A clinical photograph showing a skin lesion; a male subject age 80; the chart notes prior skin cancer (patient or family), alcohol use, no tobacco use, and no pesticide exposure; the patient is Fitzpatrick skin type I: 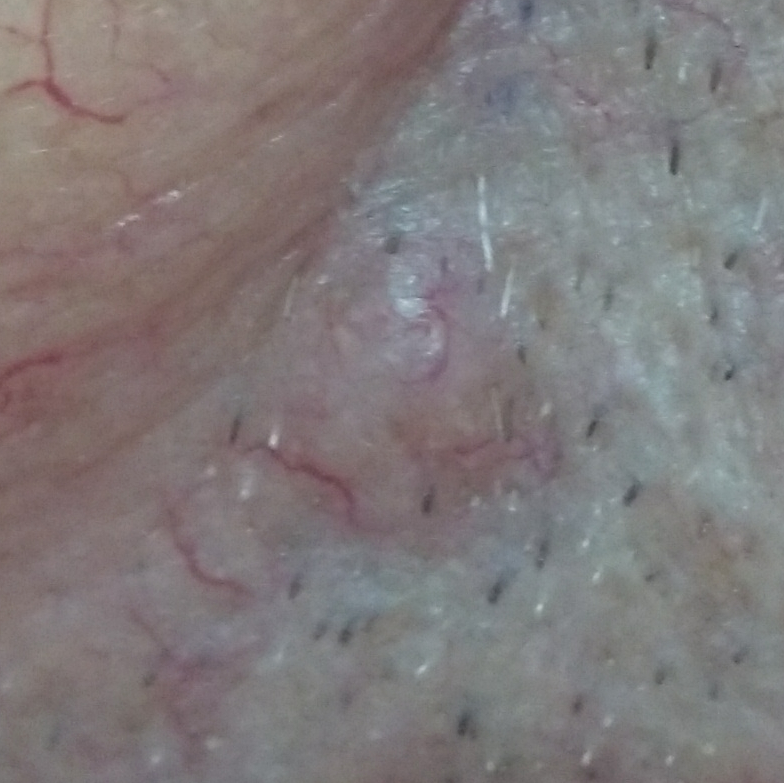Summary: The lesion involves the face. The lesion measures approximately 6 × 6 mm. The patient reports that the lesion is elevated and has grown, but does not itch. Pathology: On biopsy, the diagnosis was a basal cell carcinoma.